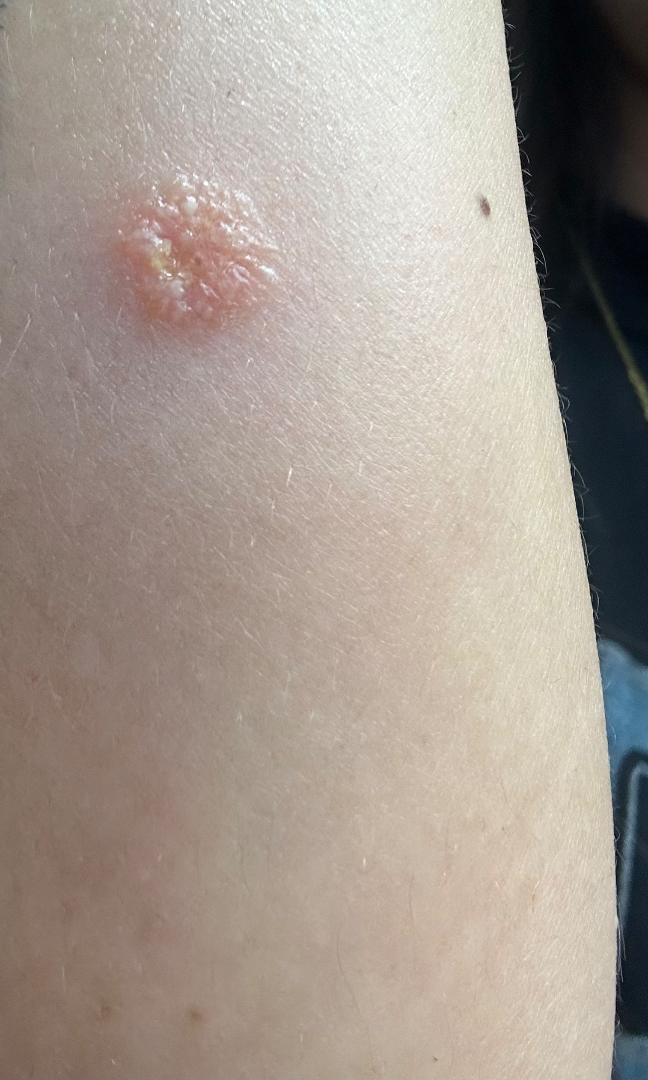No differential diagnosis could be assigned on photographic review.
Texture is reported as raised or bumpy.
This is a close-up image.